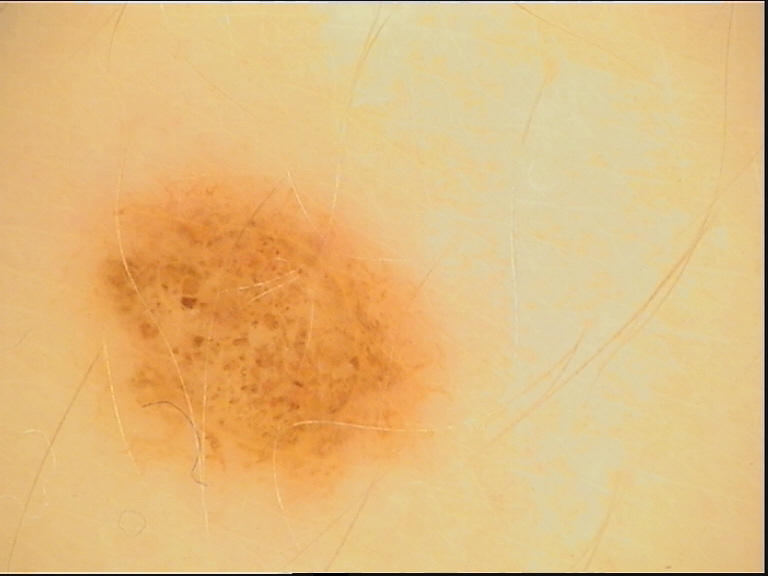  image: dermoscopy
  diagnosis:
    name: junctional nevus
    code: jb
    malignancy: benign
    super_class: melanocytic
    confirmation: expert consensus